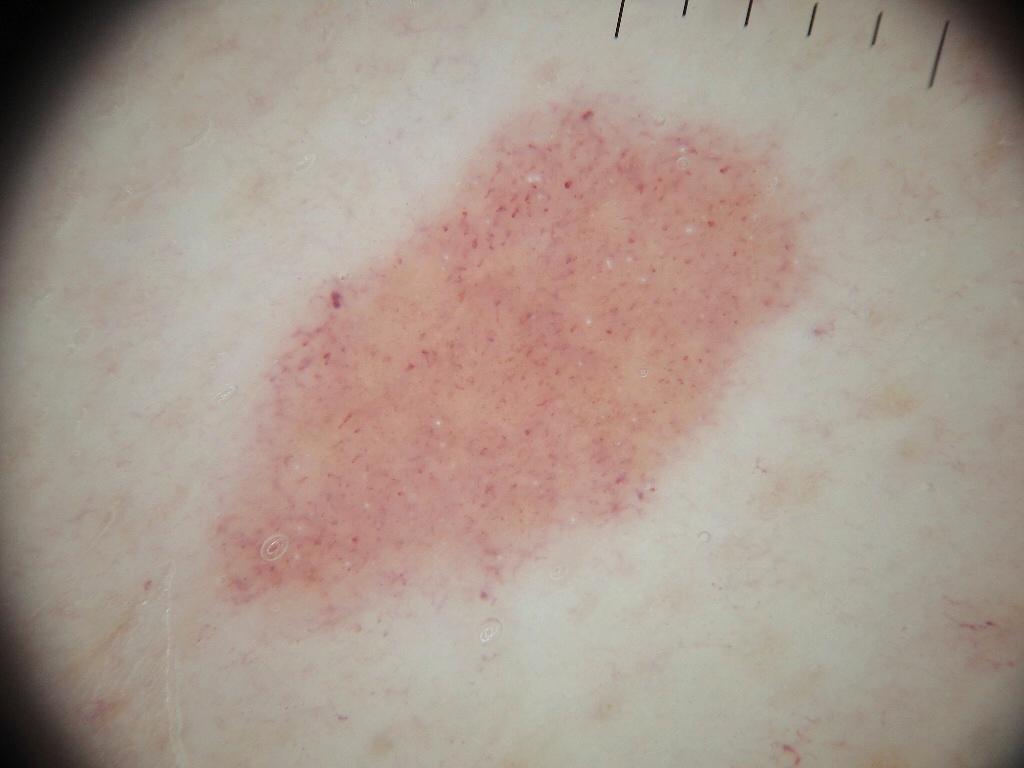Case summary:
• image type · dermoscopy of a skin lesion
• patient · male, aged approximately 75
• lesion bbox · (203, 65, 826, 647)
• dermoscopic pattern · milia-like cysts; absent: negative network, globules, streaks, and pigment network
• assessment · a melanocytic nevus, a benign skin lesion